Close-up view:
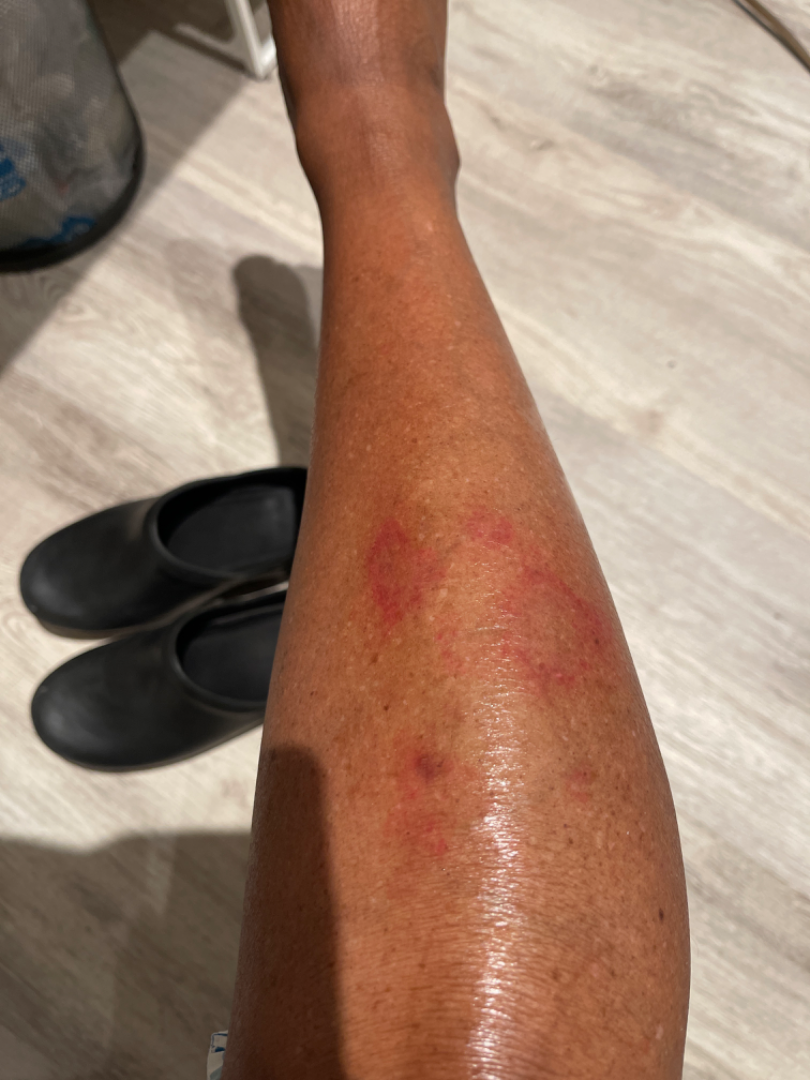| field | value |
|---|---|
| assessment | indeterminate |